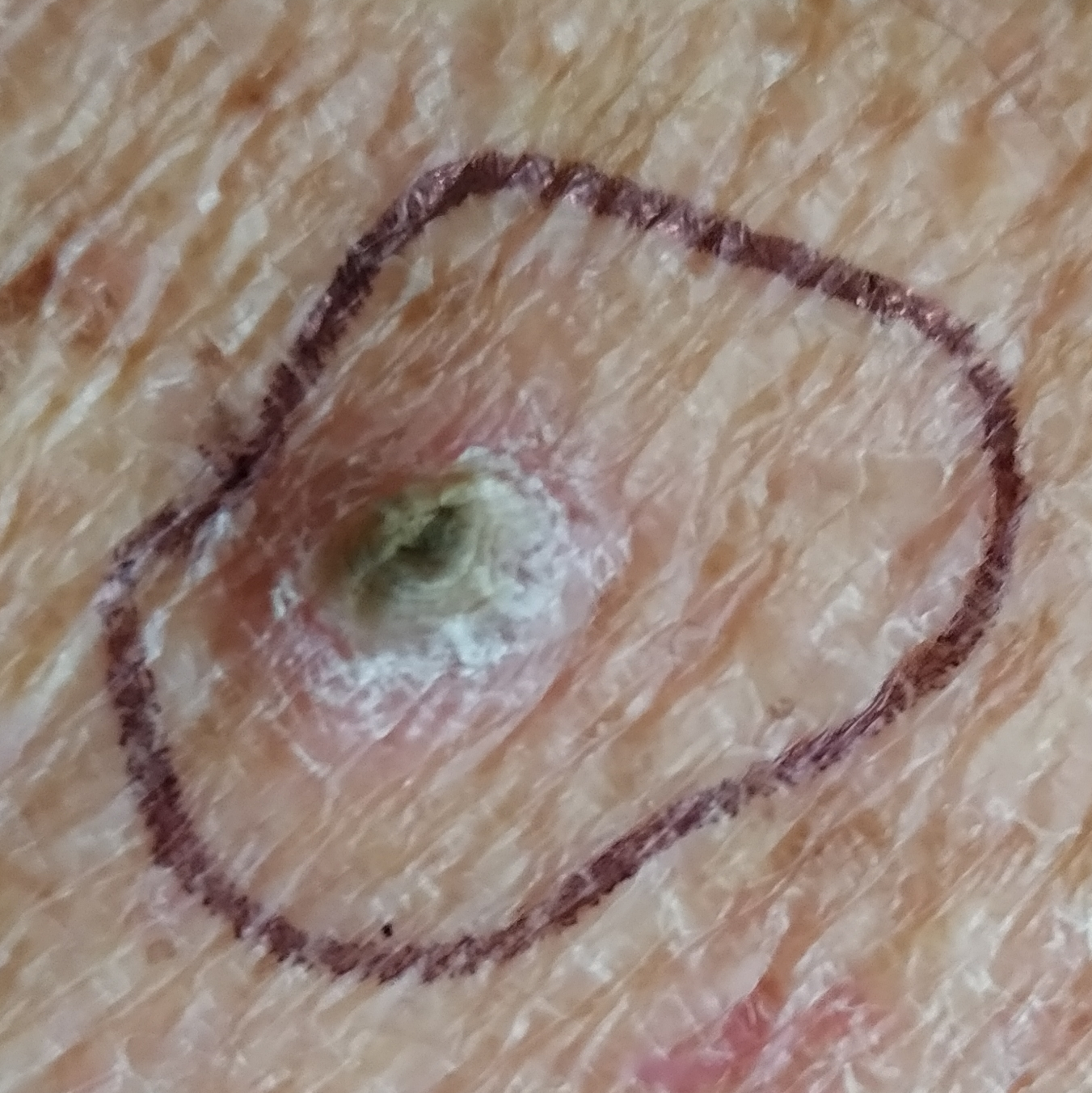Findings:
- subject — male, age 75
- risk factors — prior malignancy (patient or family), pesticide exposure
- skin phototype — II
- image — clinical photo
- location — a thigh
- diameter — 8x6 mm
- patient-reported symptoms — growth, elevation, itching
- pathology — actinic keratosis (biopsy-proven)